Dermoscopy of a skin lesion: 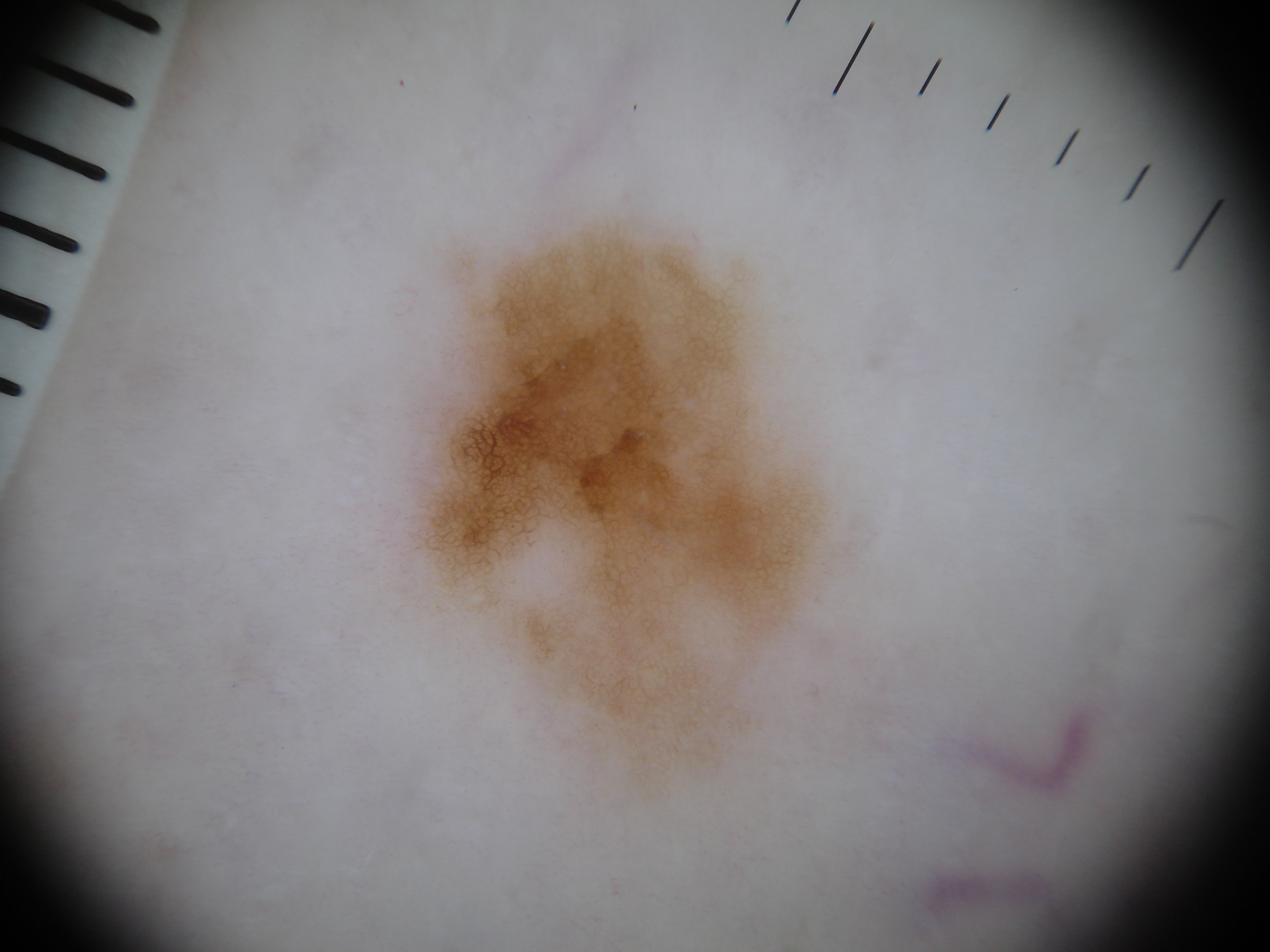<lesion>
  <lesion_location>
    <bbox_xyxy>413, 224, 826, 803</bbox_xyxy>
  </lesion_location>
  <dermoscopic_features>
    <present>pigment network</present>
    <absent>globules, streaks, negative network, milia-like cysts</absent>
  </dermoscopic_features>
  <diagnosis>
    <name>melanocytic nevus</name>
    <malignancy>benign</malignancy>
    <lineage>melanocytic</lineage>
    <provenance>clinical</provenance>
  </diagnosis>
</lesion>